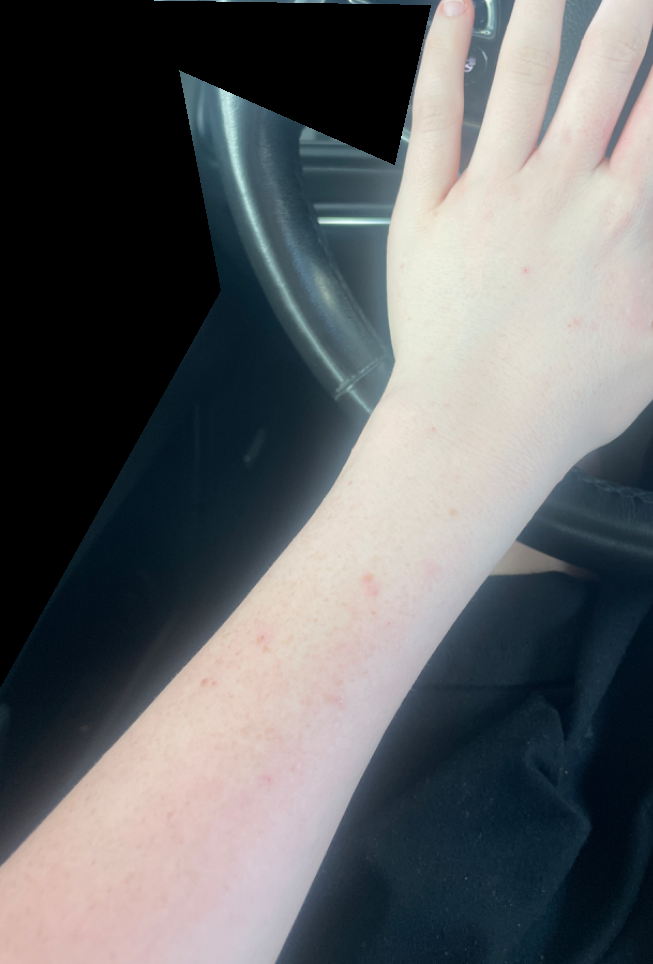Case summary:
– patient — female, age 18–29
– location — top or side of the foot, back of the hand, leg, front of the torso and arm
– photo taken — at a distance
– differential — reviewed remotely by three dermatologists: the primary impression is Eczema; with consideration of Irritant Contact Dermatitis; less probable is Lichen planus/lichenoid eruption; less likely is Allergic Contact Dermatitis